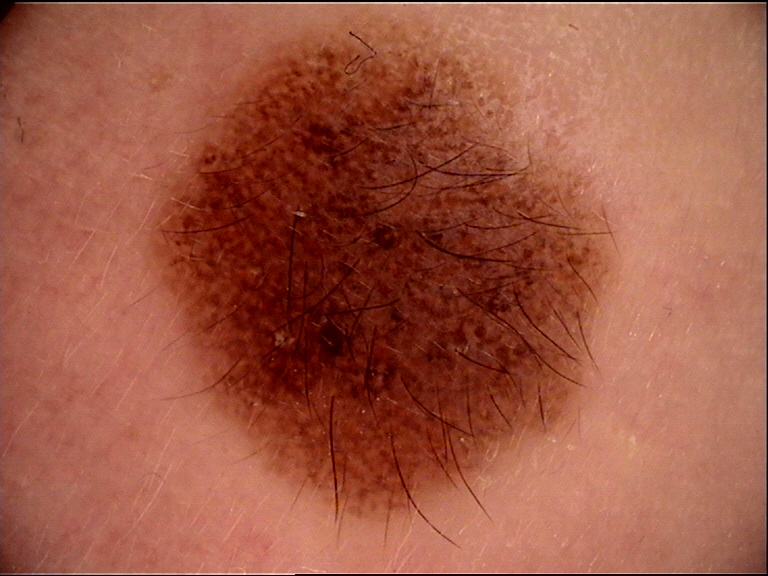The diagnosis was a congenital compound nevus.